A skin lesion imaged with a dermatoscope; the patient is a male aged 48 to 52: 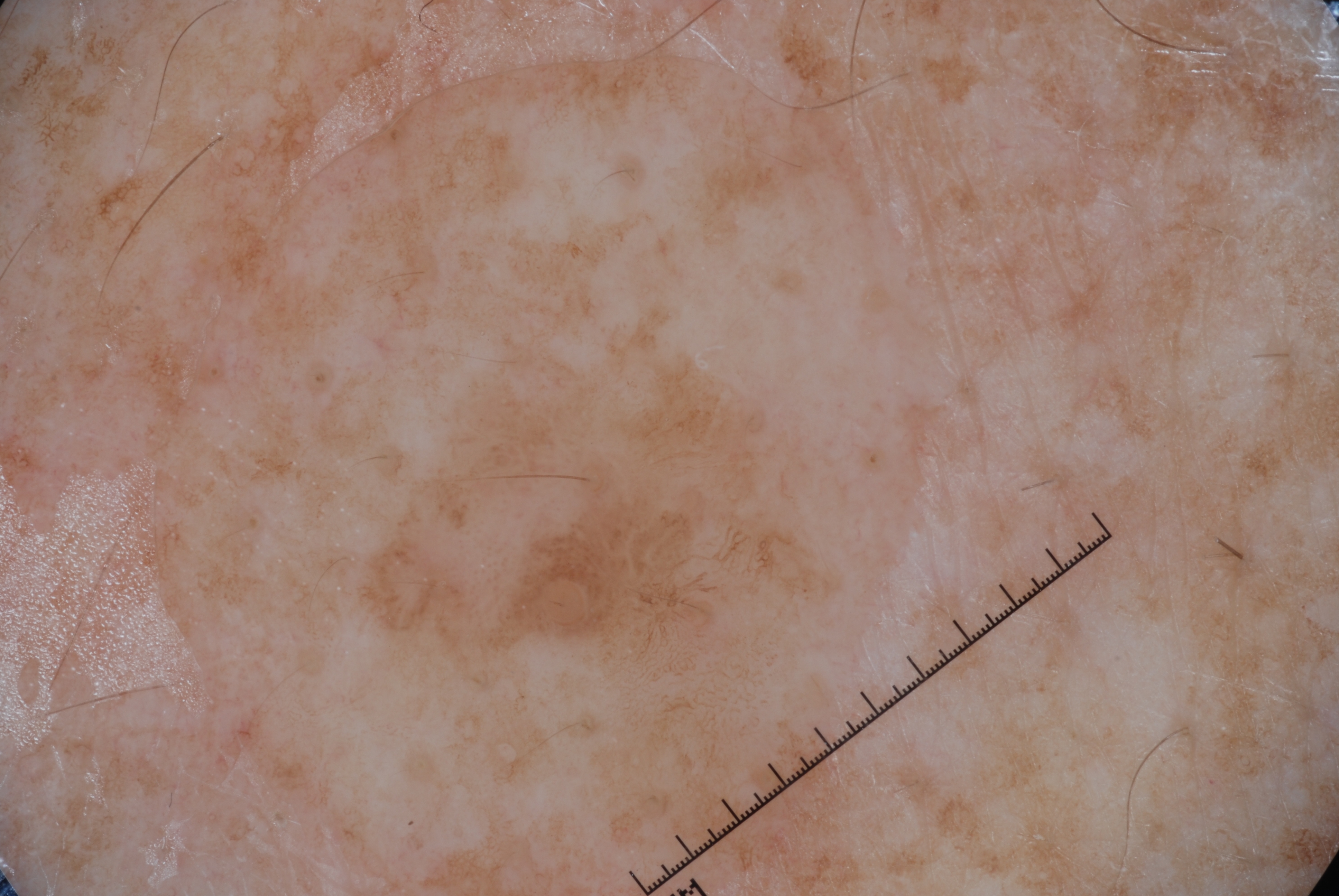Summary:
In (x1, y1, x2, y2) order, the lesion spans 348/307/845/856. Dermoscopic examination shows pigment network, with no streaks, negative network, or milia-like cysts.
Conclusion:
The lesion was assessed as a seborrheic keratosis.